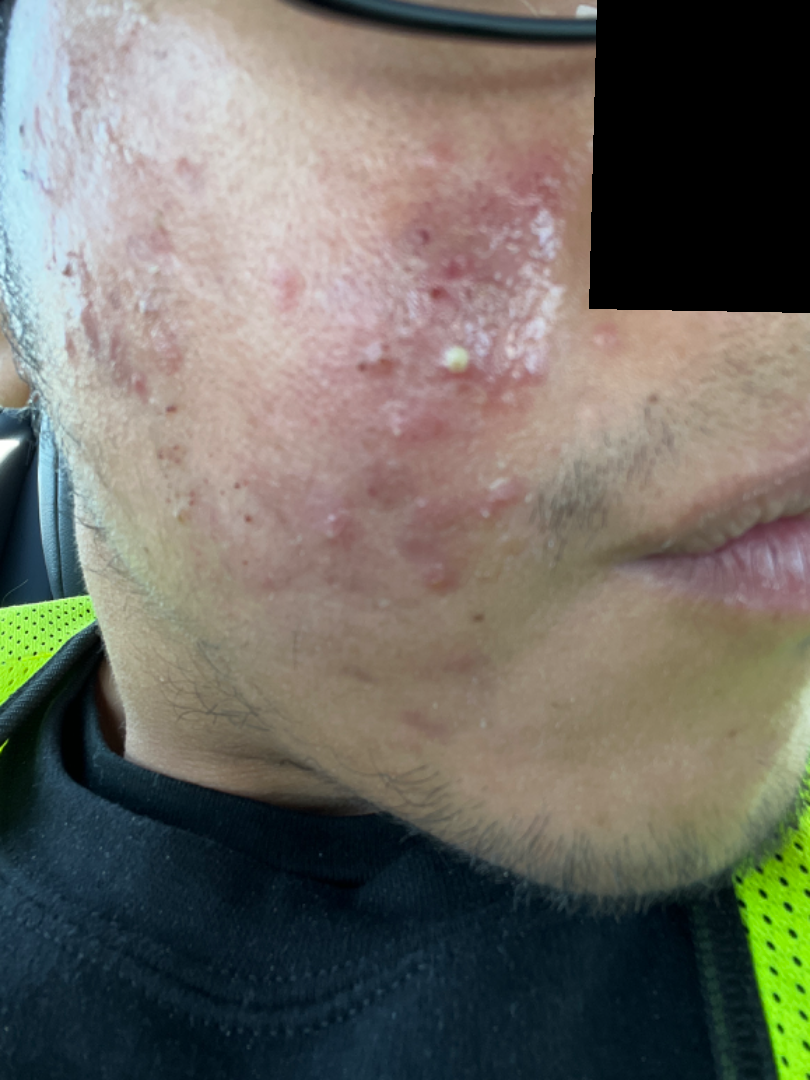<report>
  <body_site>head or neck</body_site>
  <patient>male, age 18–29</patient>
  <shot_type>close-up</shot_type>
  <differential>Acne</differential>
</report>